A female subject 58 years of age · a clinical photo of a skin lesion taken with a smartphone — 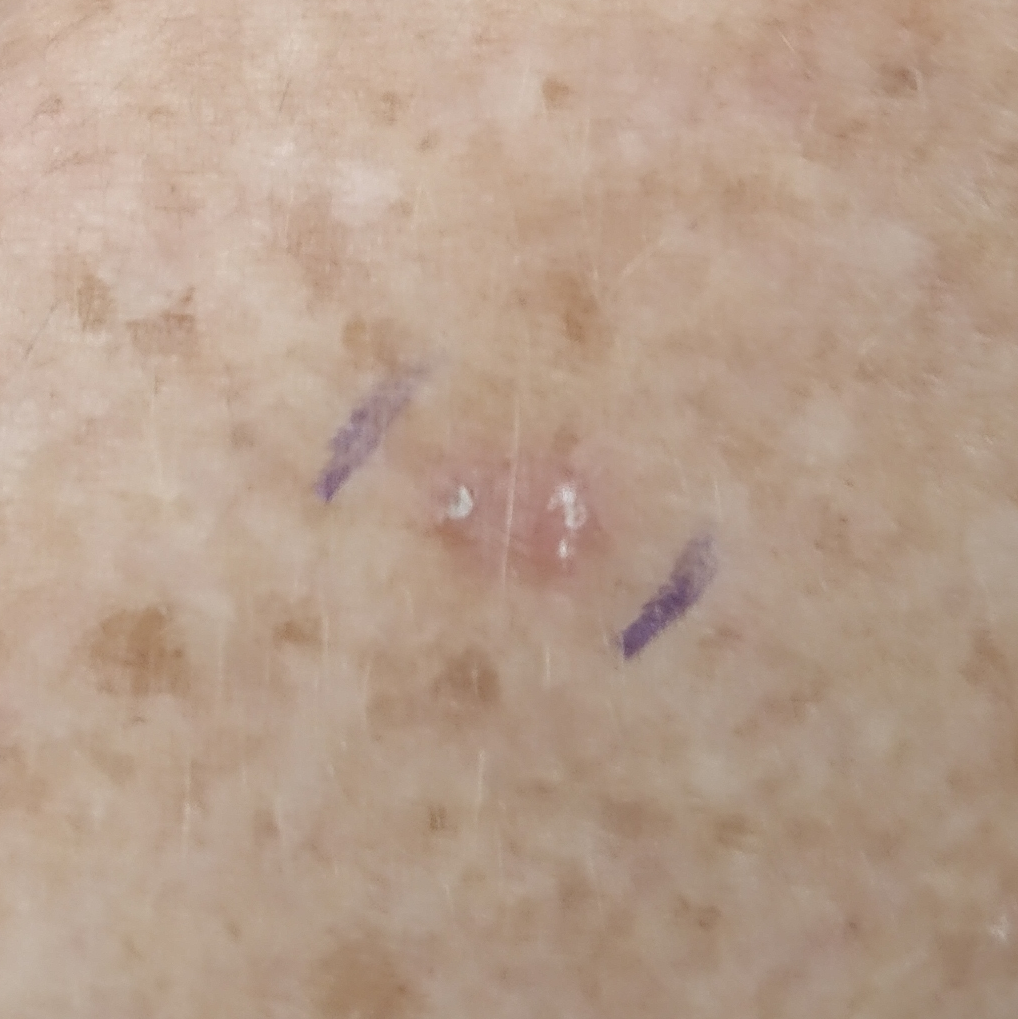Q: Where on the body is the lesion?
A: a forearm
Q: What is this lesion?
A: actinic keratosis (clinical consensus)